A dermoscopic close-up of a skin lesion.
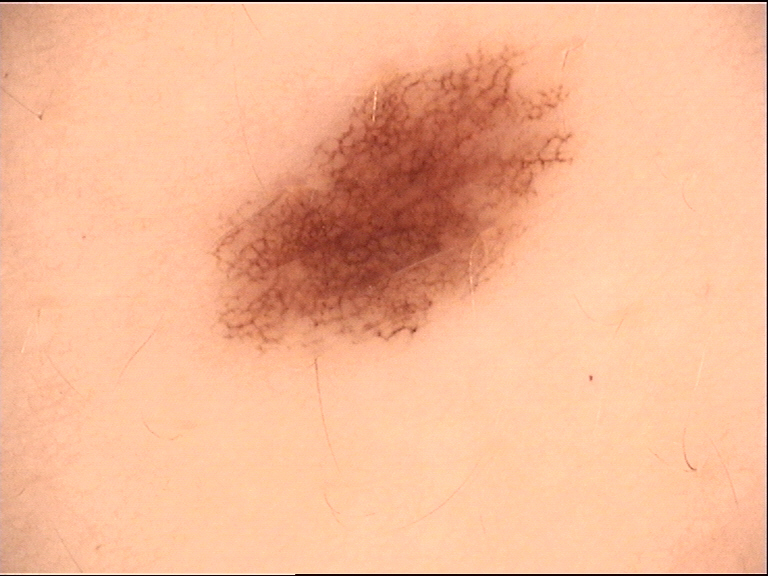Labeled as a banal lesion — a junctional nevus.